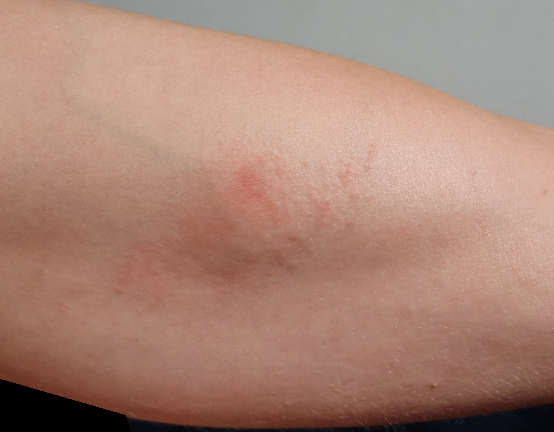Background:
The lesion involves the arm. This image was taken at a distance.
Findings:
Most consistent with Allergic Contact Dermatitis.